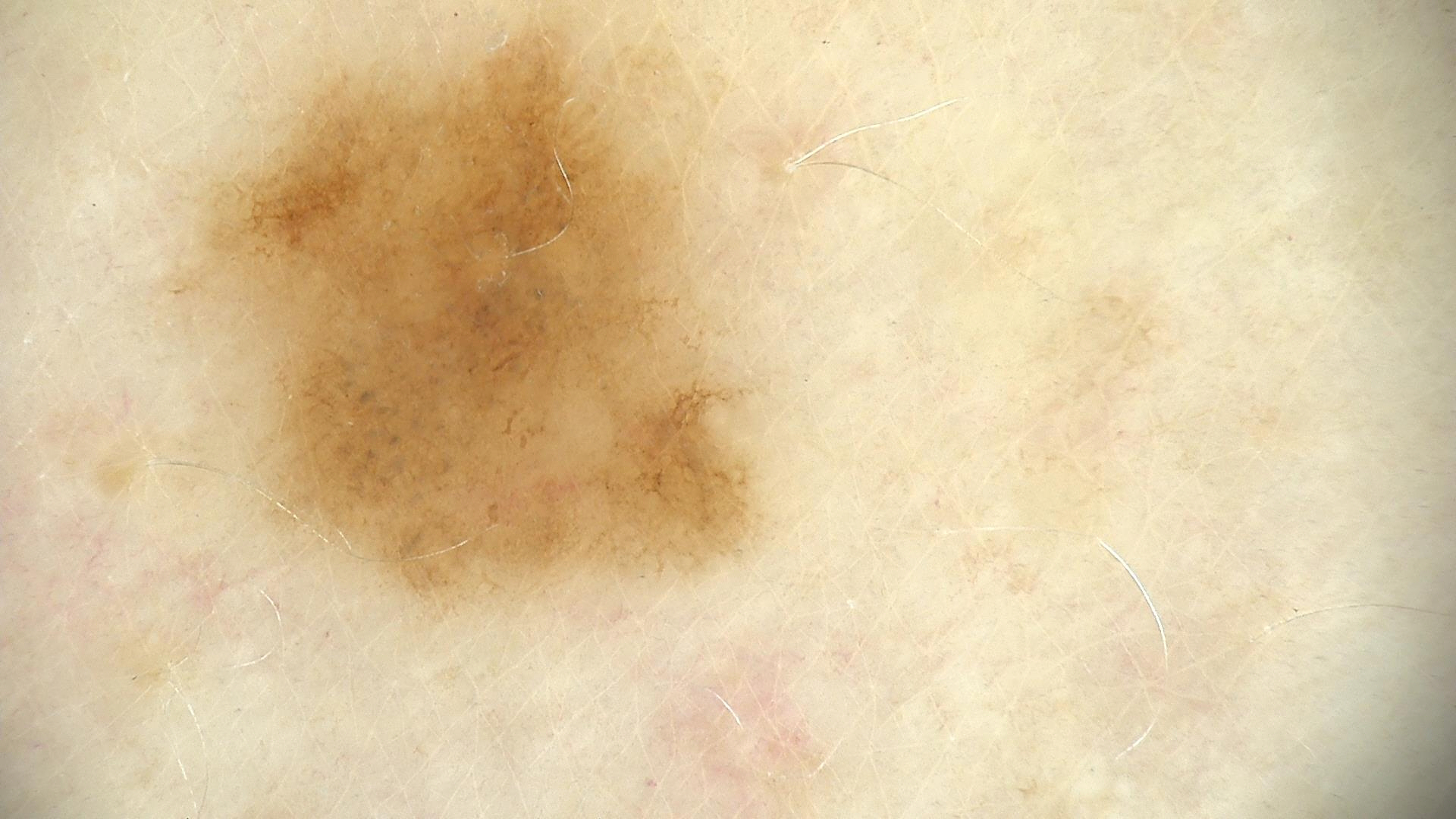Consistent with a dysplastic junctional nevus.